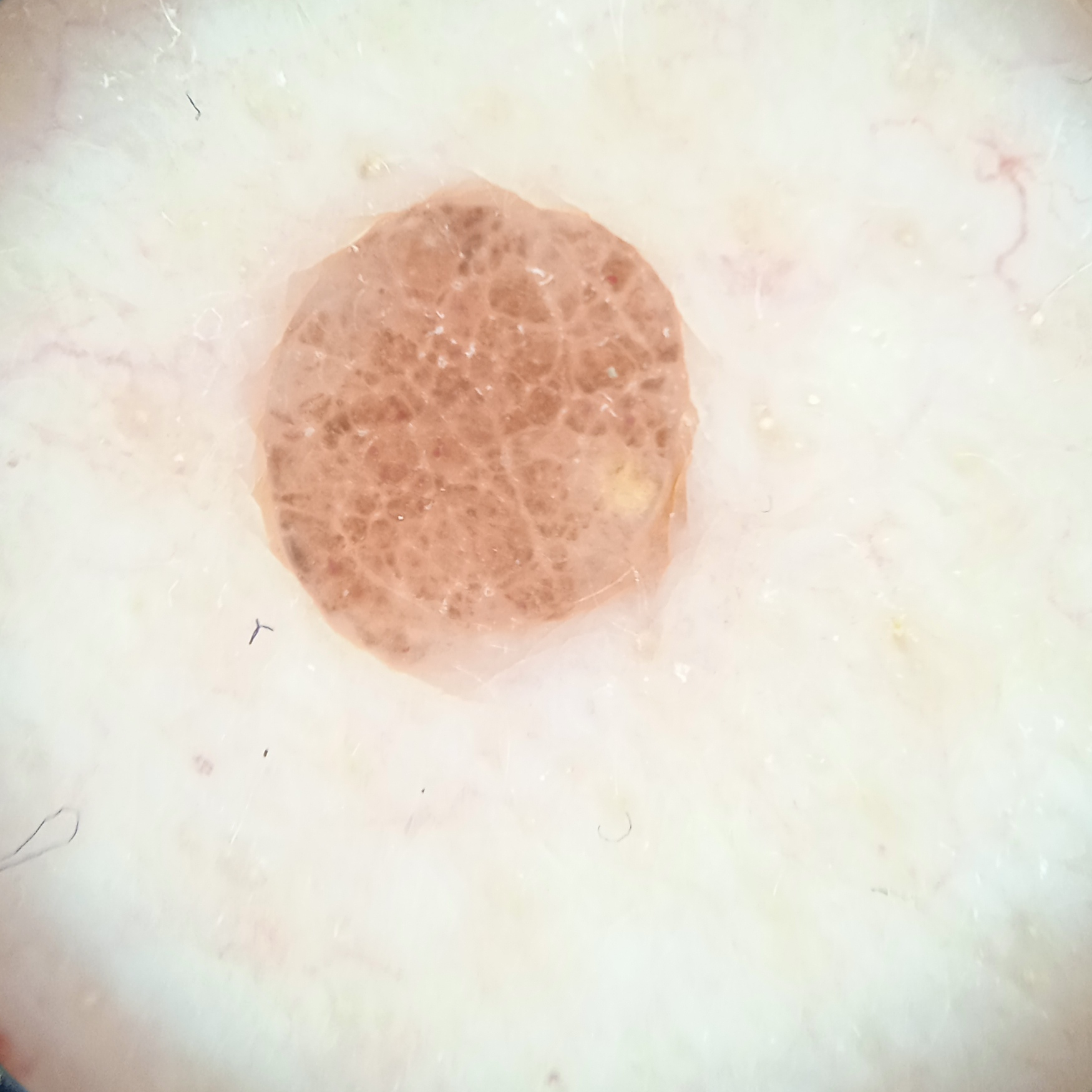Case:
- subject: male, 65 years old
- modality: dermatoscopic image
- clinical context: research study (no referral diagnosis)
- nevus count: numerous melanocytic nevi
- sun reaction: skin reddens painfully with sun exposure
- diameter: 3 mm
- diagnostic label: melanocytic nevus (dermatologist consensus)